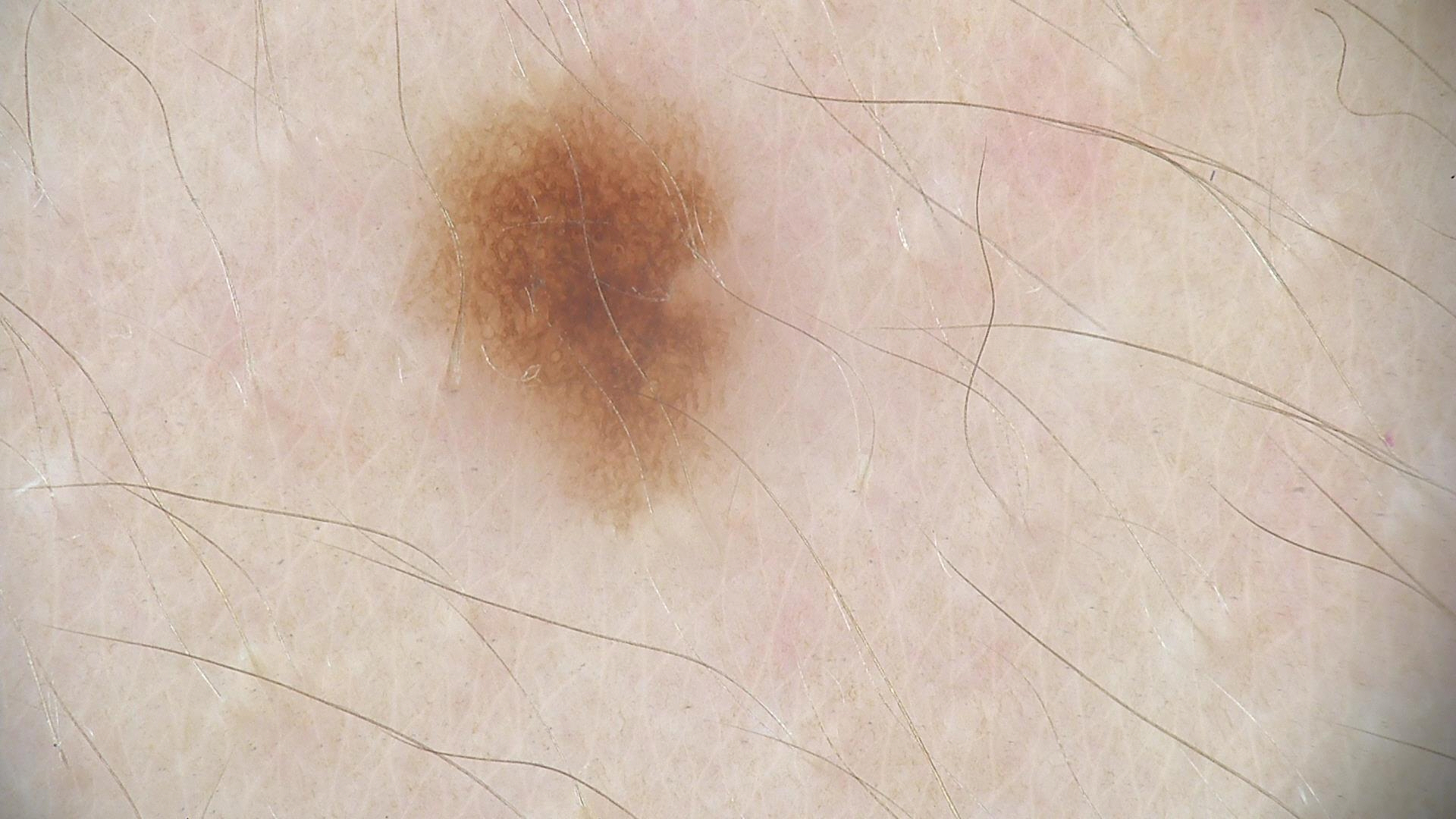imaging — dermatoscopy
label — dysplastic junctional nevus (expert consensus)